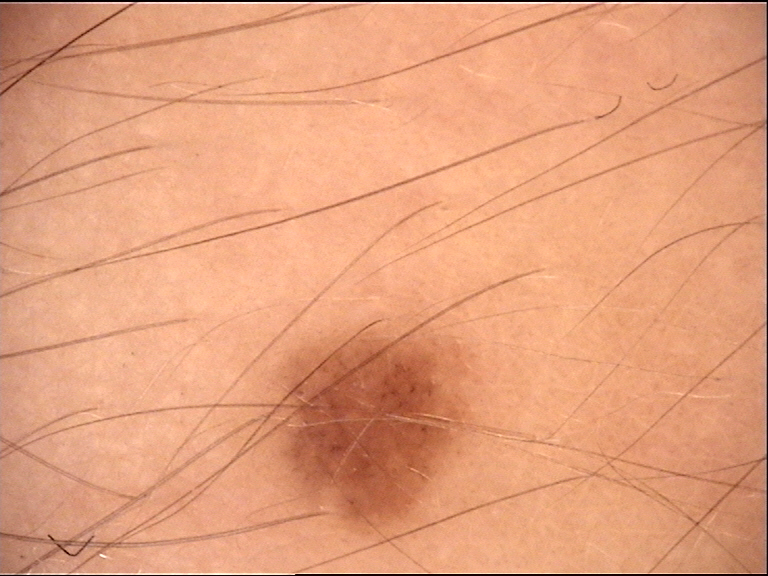class — junctional nevus (expert consensus)